A clinical photograph showing a skin lesion. A female patient 50 years old. Imaged for a research study, with no referral diagnosis recorded.
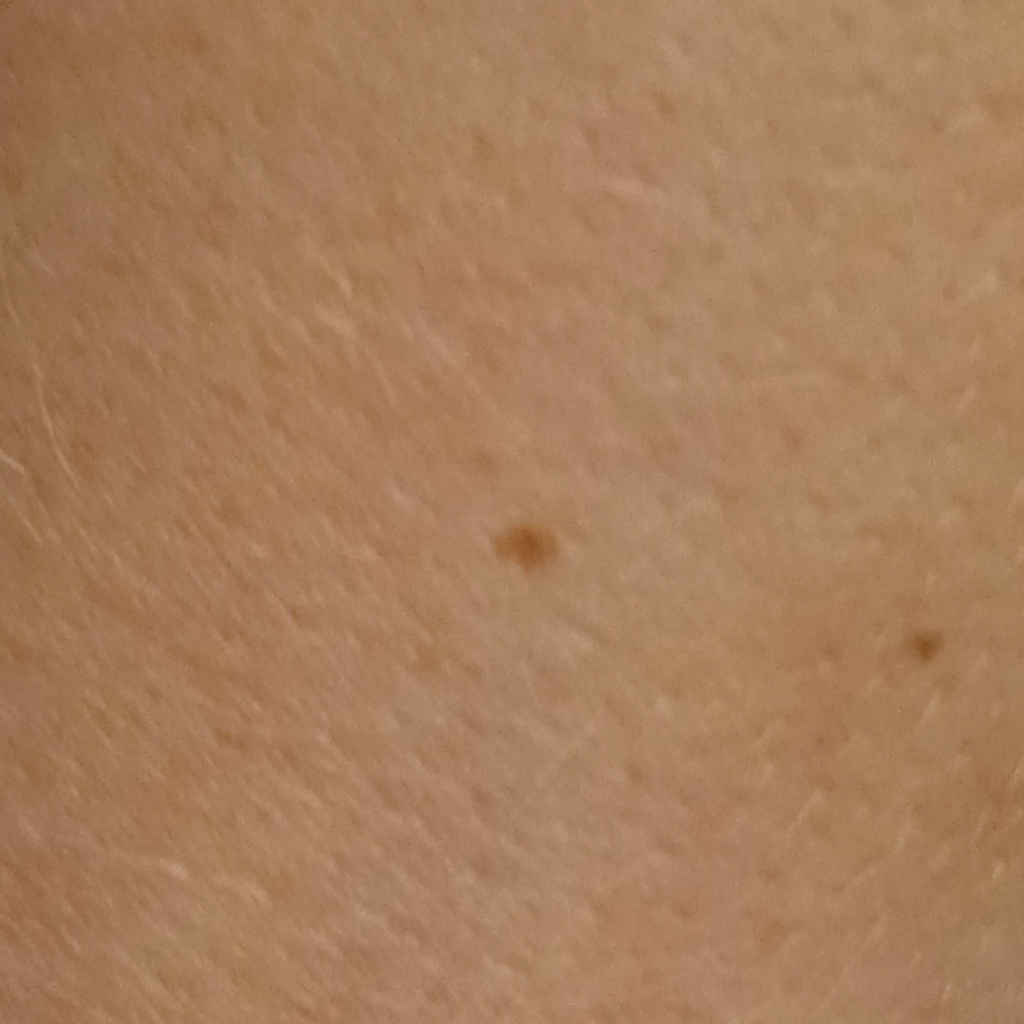| feature | finding |
|---|---|
| site | an arm |
| assessment | melanocytic nevus (dermatologist consensus) |